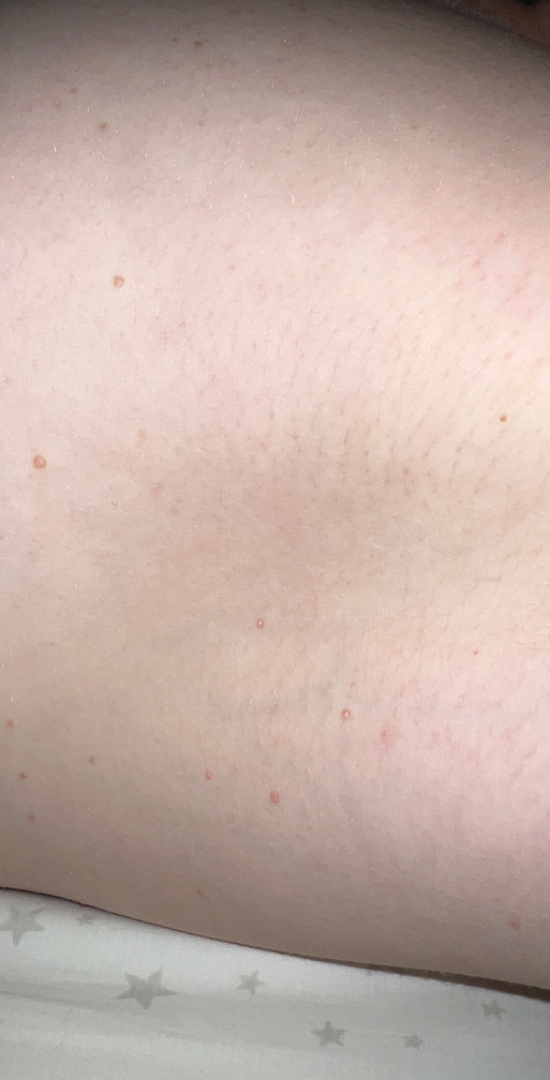Clinical context: This is a close-up image. Assessment: On photographic review: most likely Molluscum Contagiosum; also raised was Verruca vulgaris; possibly Folliculitis.